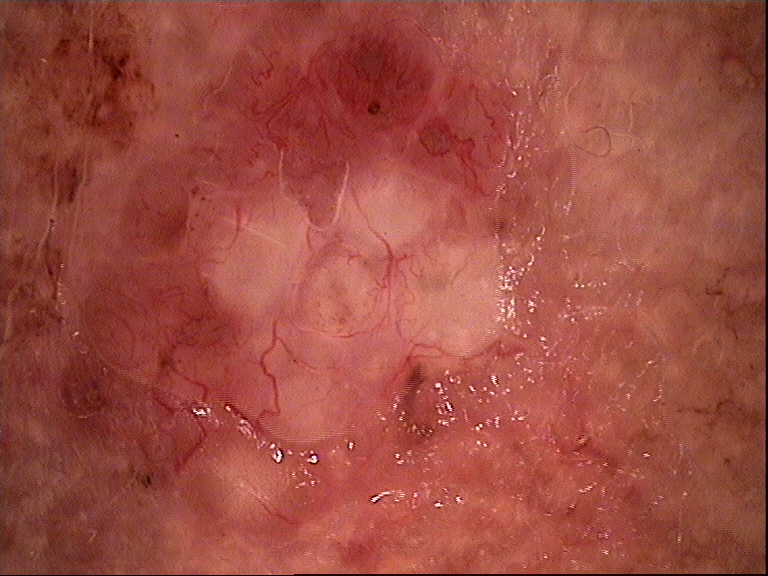Biopsy-confirmed as a basal cell carcinoma.